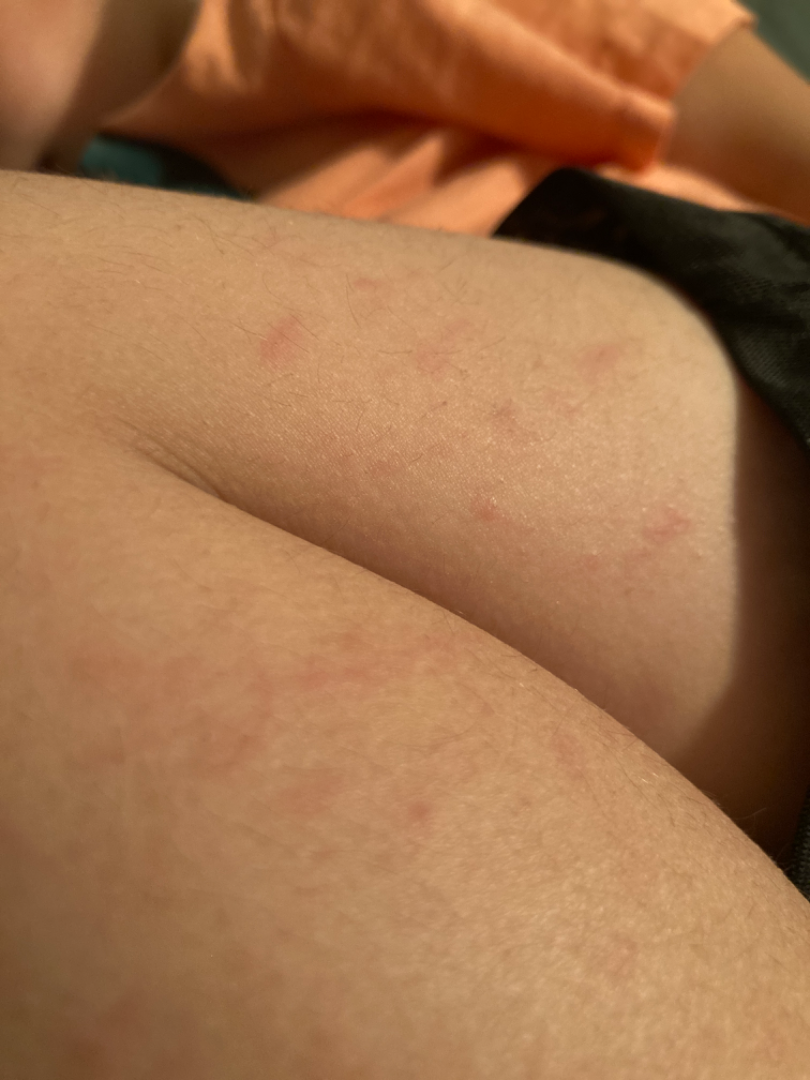Findings: The reviewer was unable to grade this case for skin condition. Background: This image was taken at an angle.